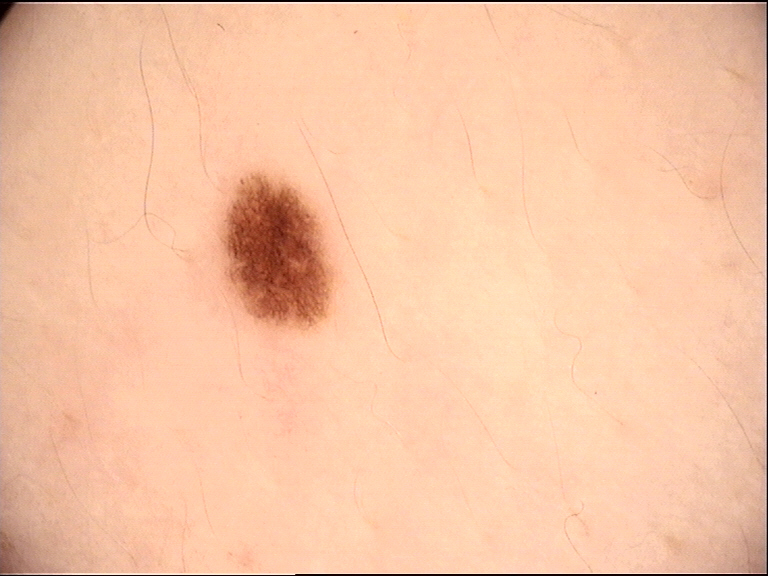Q: What kind of image is this?
A: dermatoscopy
Q: What is the lesion category?
A: banal
Q: What is this lesion?
A: junctional nevus (expert consensus)